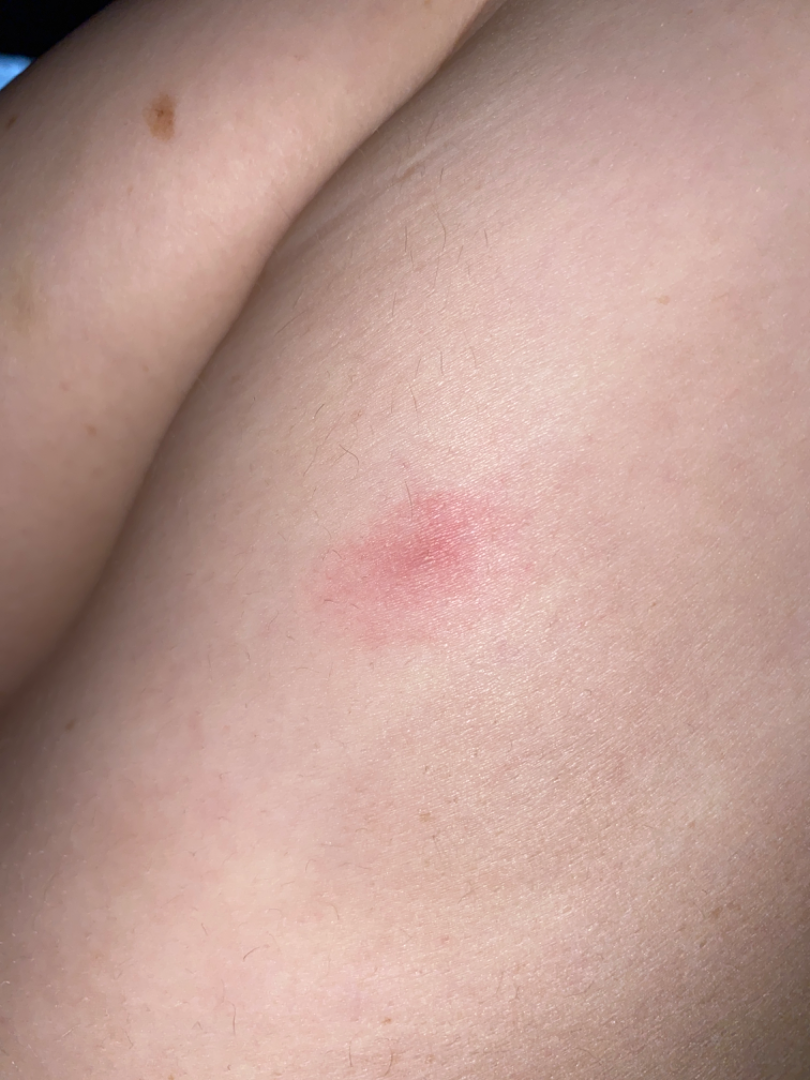The dermatologist could not determine a likely condition from the photograph alone.